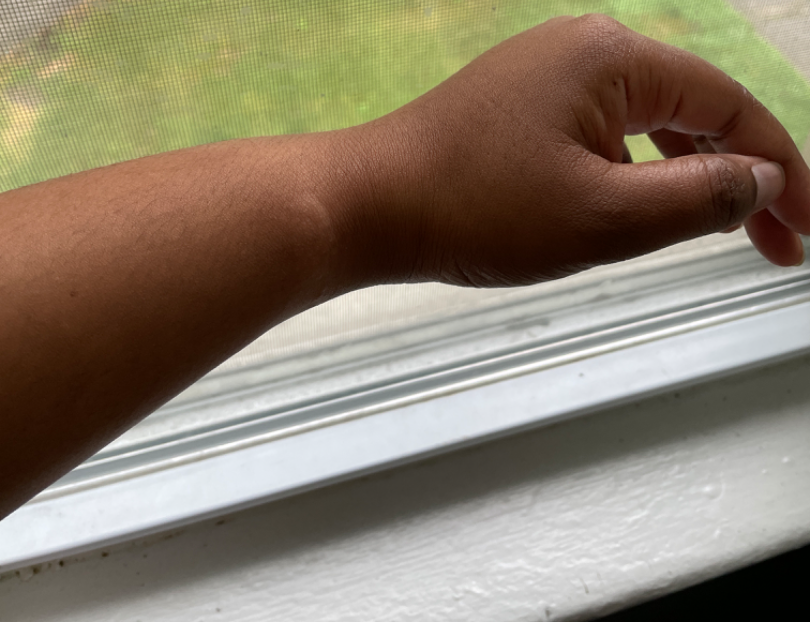Review:
On remote review of the image, Contact dermatitis, Eczema and Acute and chronic dermatitis were each considered, in no particular order.